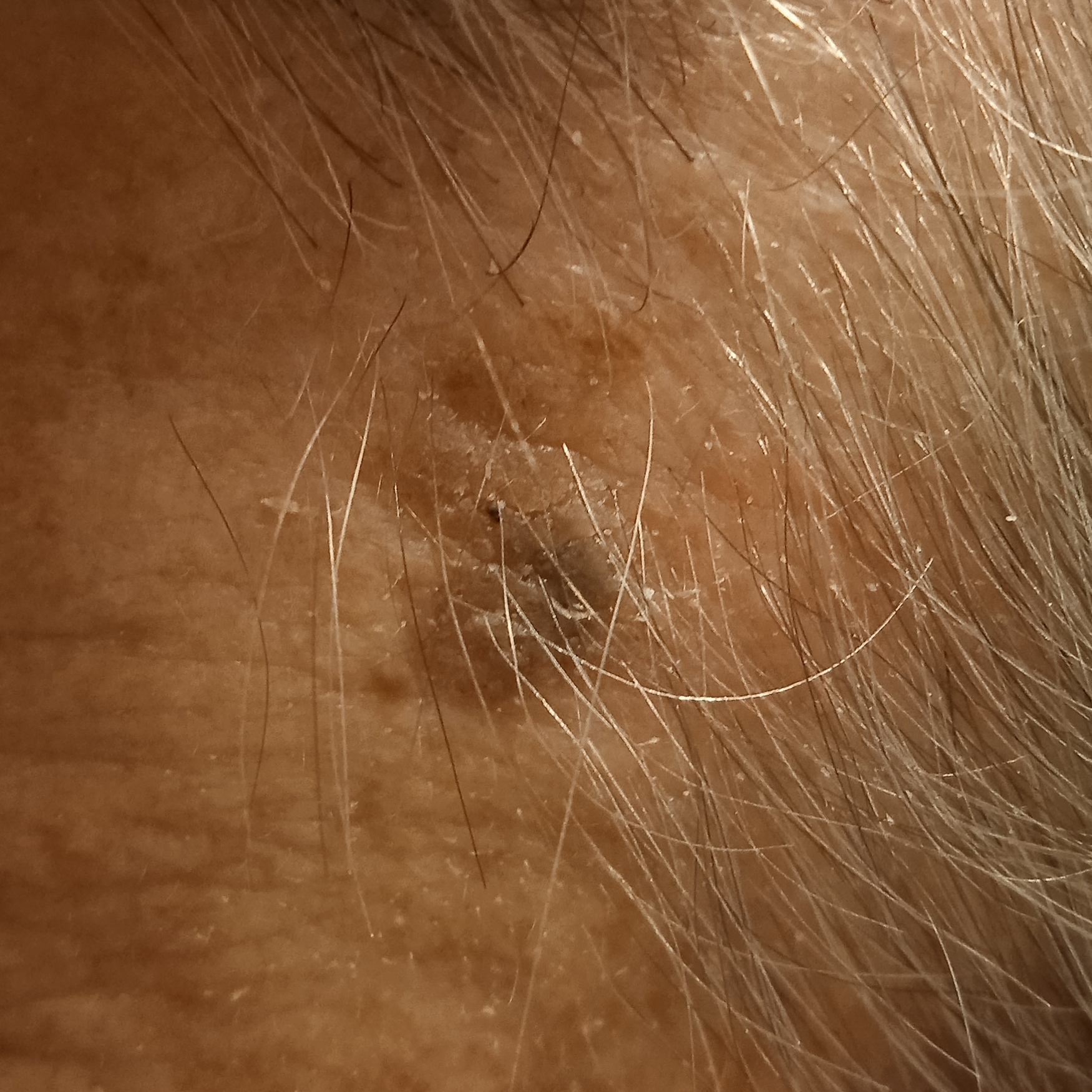Q: Why was this imaged?
A: research study (no referral diagnosis)
Q: Where is the lesion?
A: an arm
Q: What was the diagnosis?
A: seborrheic keratosis (dermatologist consensus)